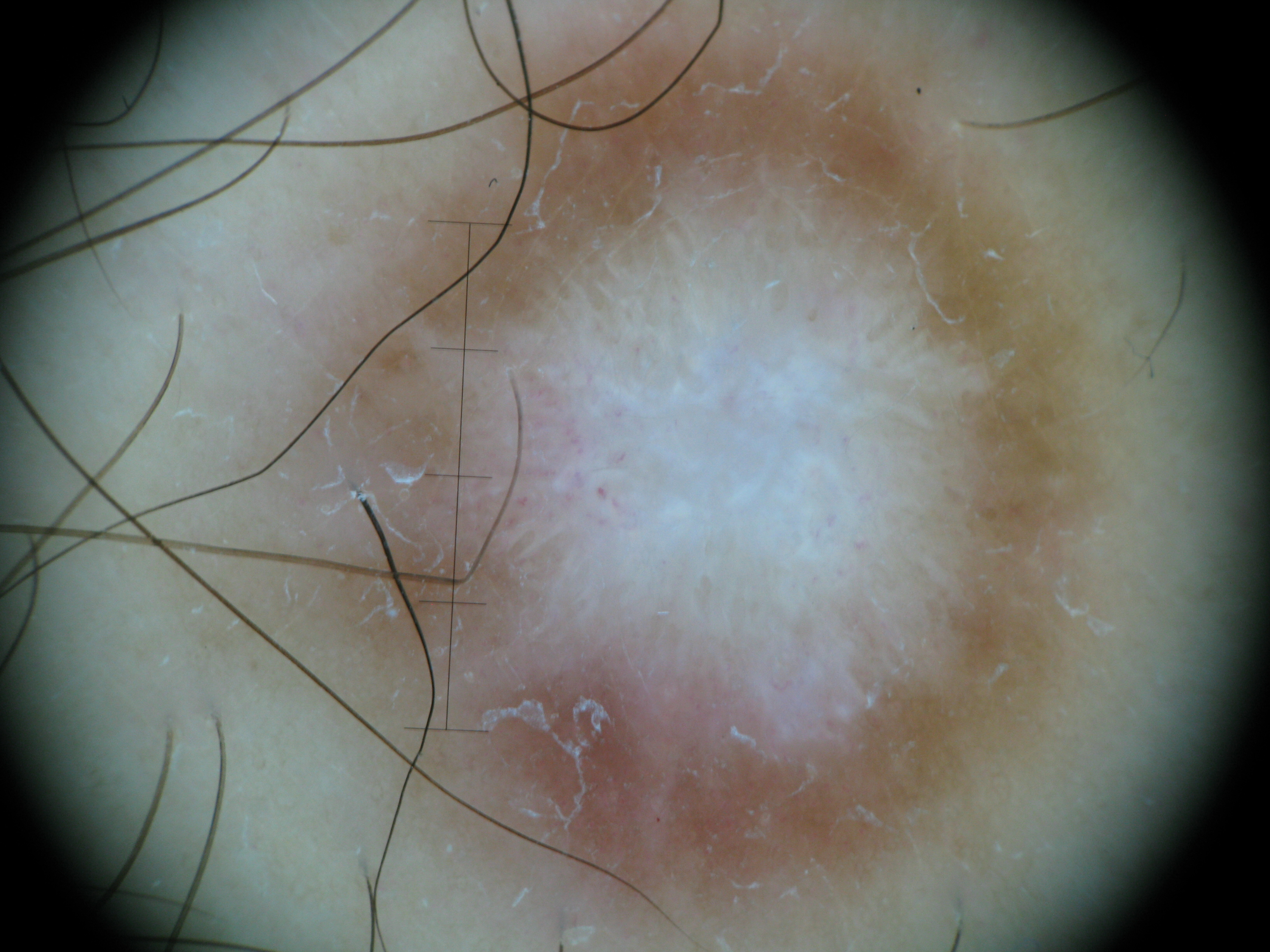A dermoscopic close-up of a skin lesion.
This is a fibro-histiocytic lesion.
The diagnosis was a benign lesion — a dermatofibroma.